A skin lesion imaged with a dermatoscope: 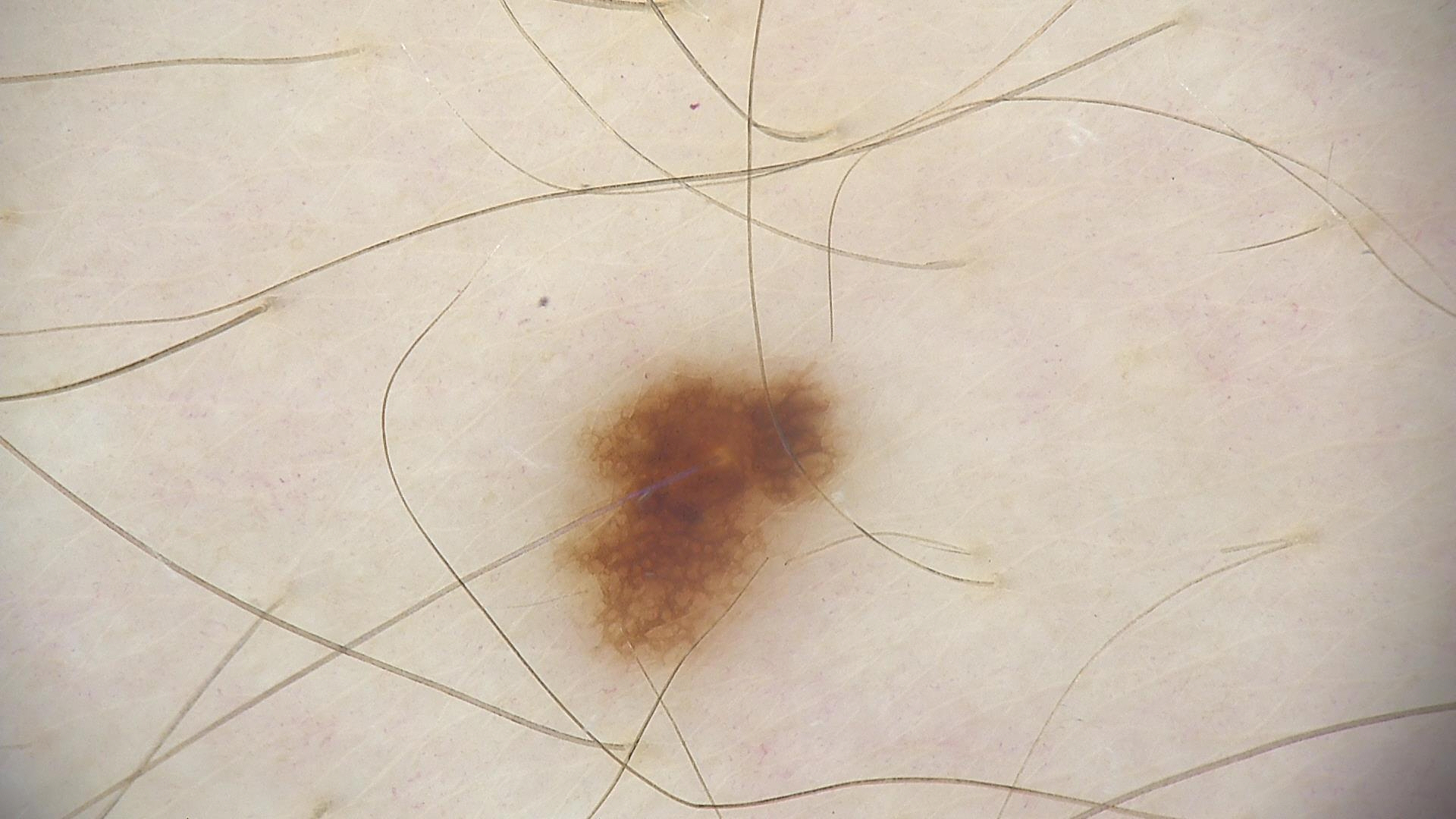Impression: Classified as a dysplastic junctional nevus.